A dermoscopic close-up of a skin lesion. The patient is a female aged 33-37:
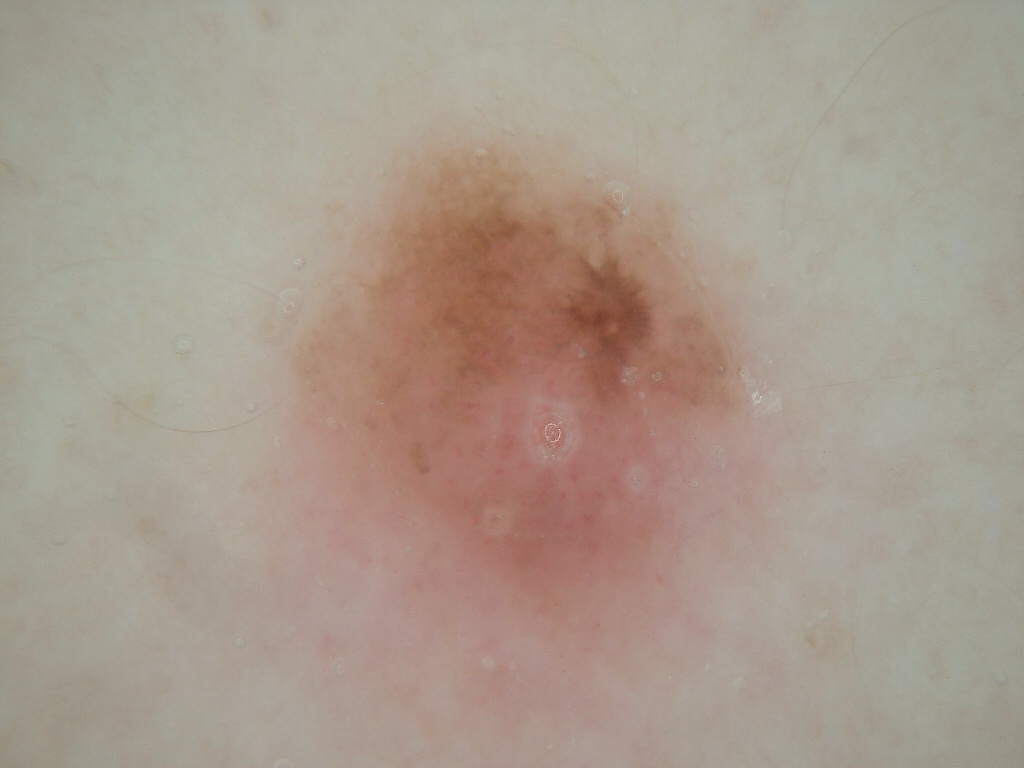Q: What is the lesion's bounding box?
A: left=257, top=115, right=785, bottom=755
Q: Which dermoscopic features were noted?
A: milia-like cysts and pigment network; absent: streaks and negative network
Q: Lesion extent?
A: large
Q: What did the assessment conclude?
A: a melanocytic nevus